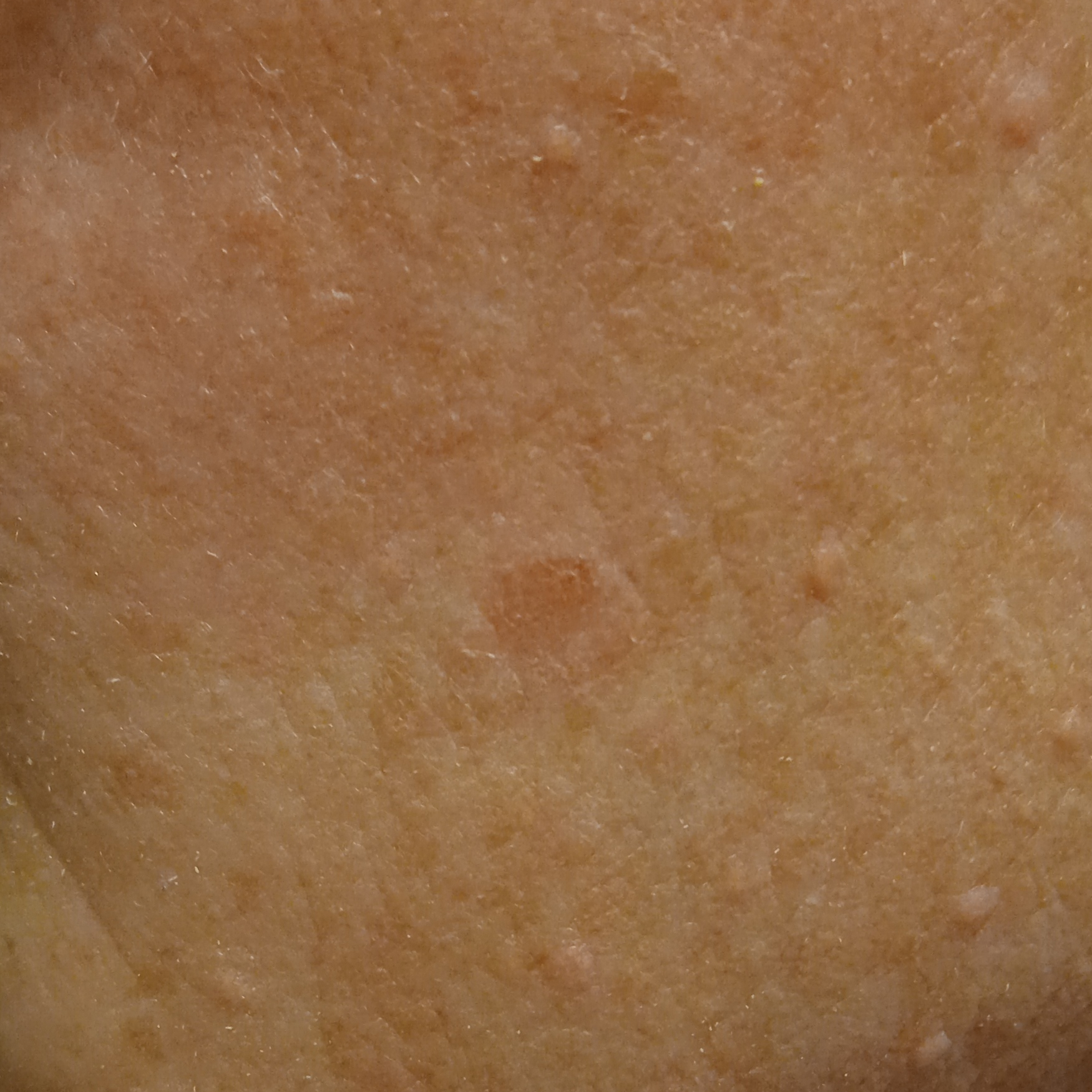A female patient 55 years of age. A clinical photograph showing a skin lesion. The lesion is located on the face. Measuring roughly 5.7 mm. The consensus diagnosis for this lesion was an actinic keratosis.